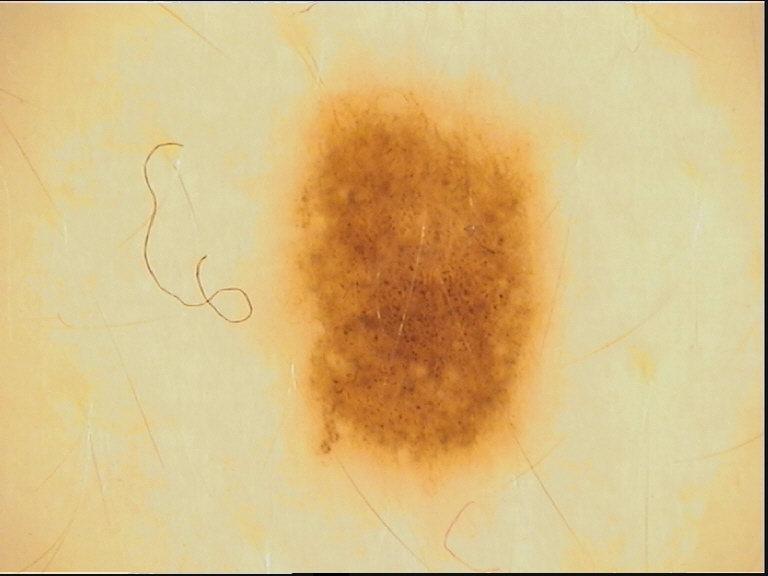{
  "image": "dermatoscopy",
  "diagnosis": {
    "name": "dysplastic junctional nevus",
    "code": "jd",
    "malignancy": "benign",
    "super_class": "melanocytic",
    "confirmation": "expert consensus"
  }
}